Fitzpatrick skin type II. A female subject aged around 85 or older — 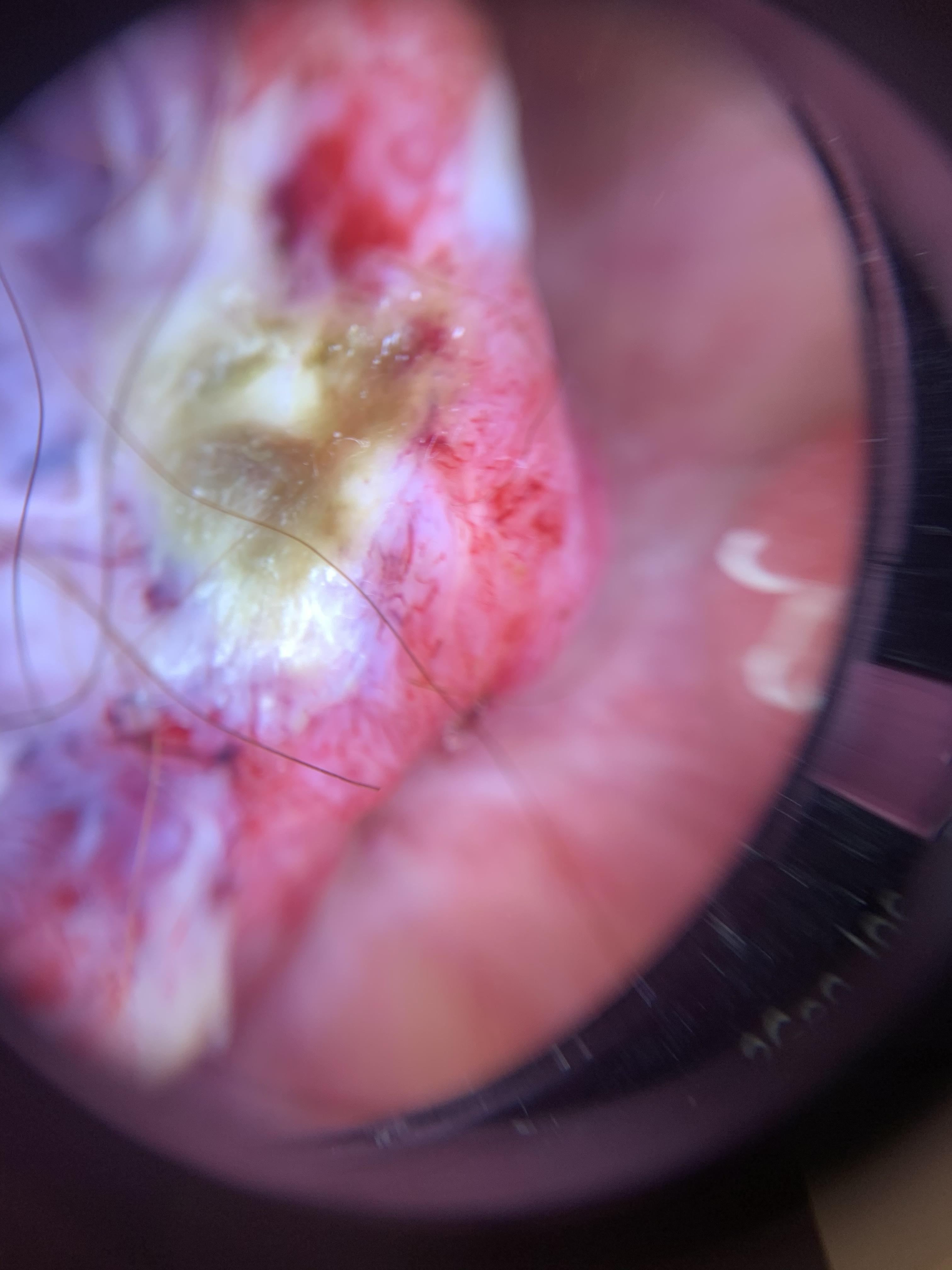Diagnosis:
Histopathological examination showed a malignant, epidermal lesion — a squamous cell carcinoma.